A dermoscopic photograph of a skin lesion: 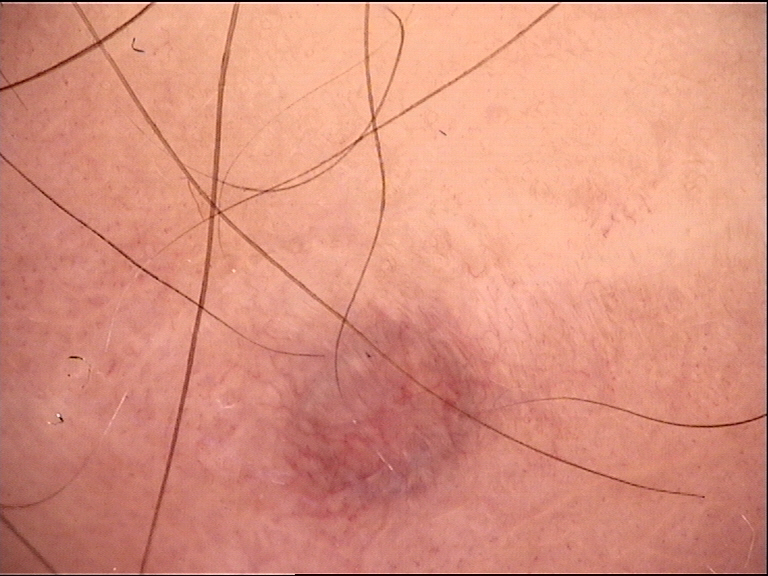{
  "lesion_type": {
    "main_class": "banal",
    "pattern": "dermal"
  },
  "diagnosis": {
    "name": "blue nevus",
    "code": "bdb",
    "malignancy": "benign",
    "super_class": "melanocytic",
    "confirmation": "expert consensus"
  }
}